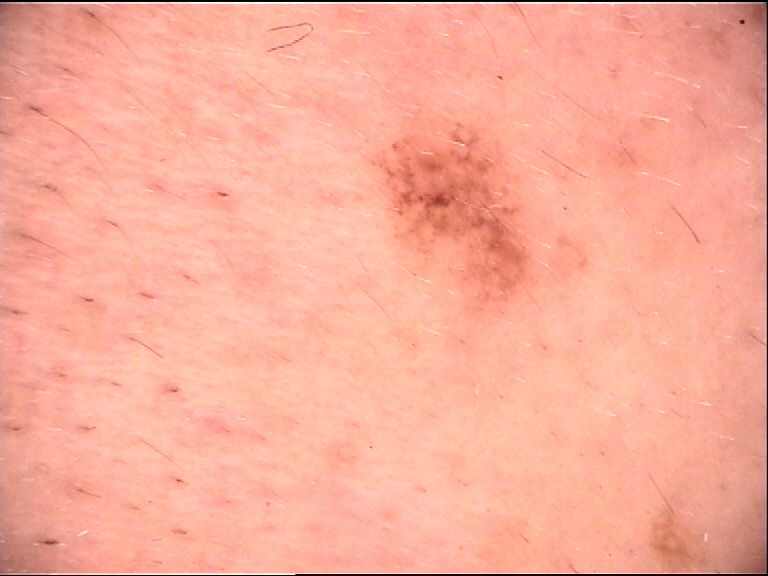The architecture is that of a compound, banal lesion.
Labeled as a Miescher nevus.